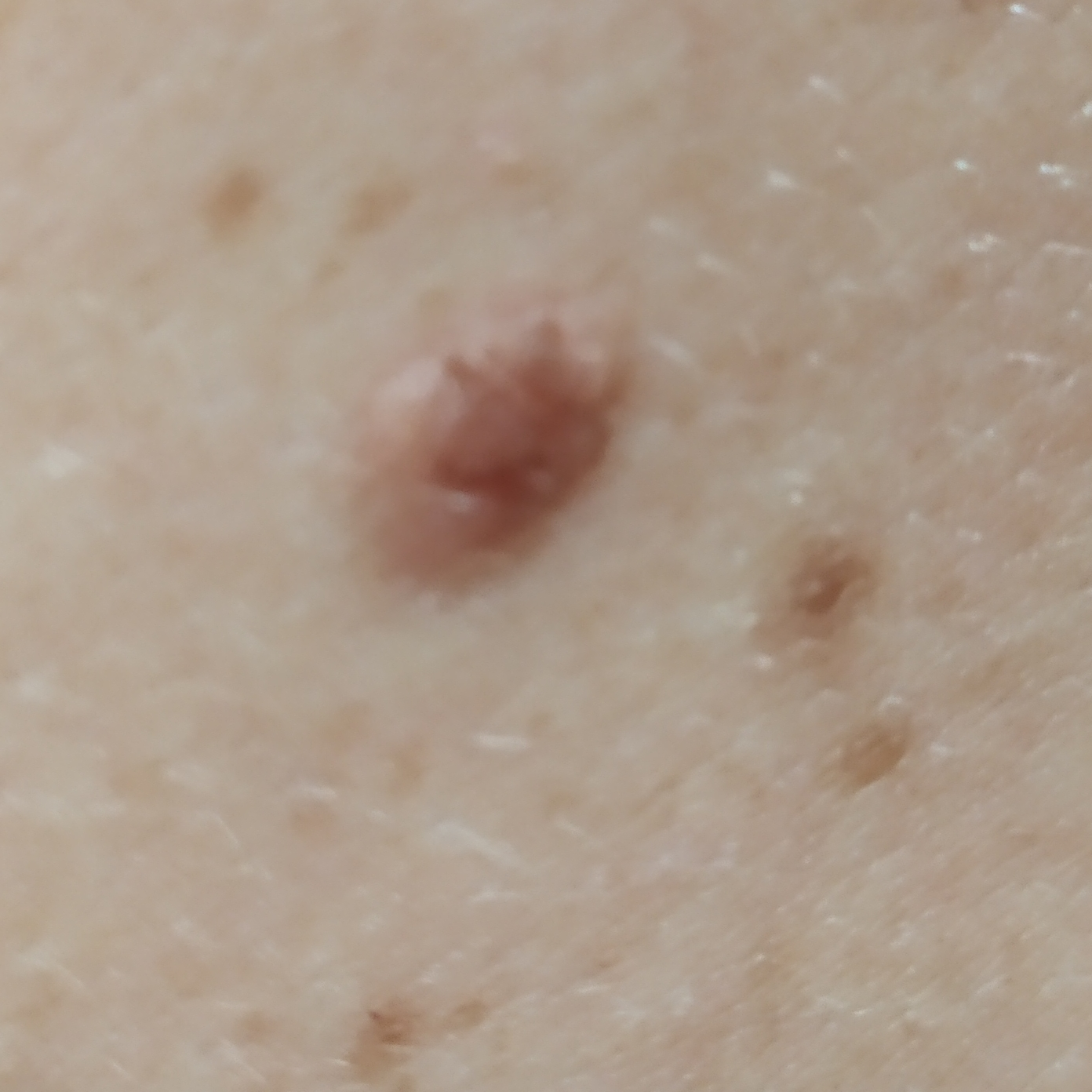Findings: A patient in their 30s. A clinical photograph of a skin lesion. Located on the back. No symptoms reported. Conclusion: The diagnostic impression was a benign skin lesion — a seborrheic keratosis.